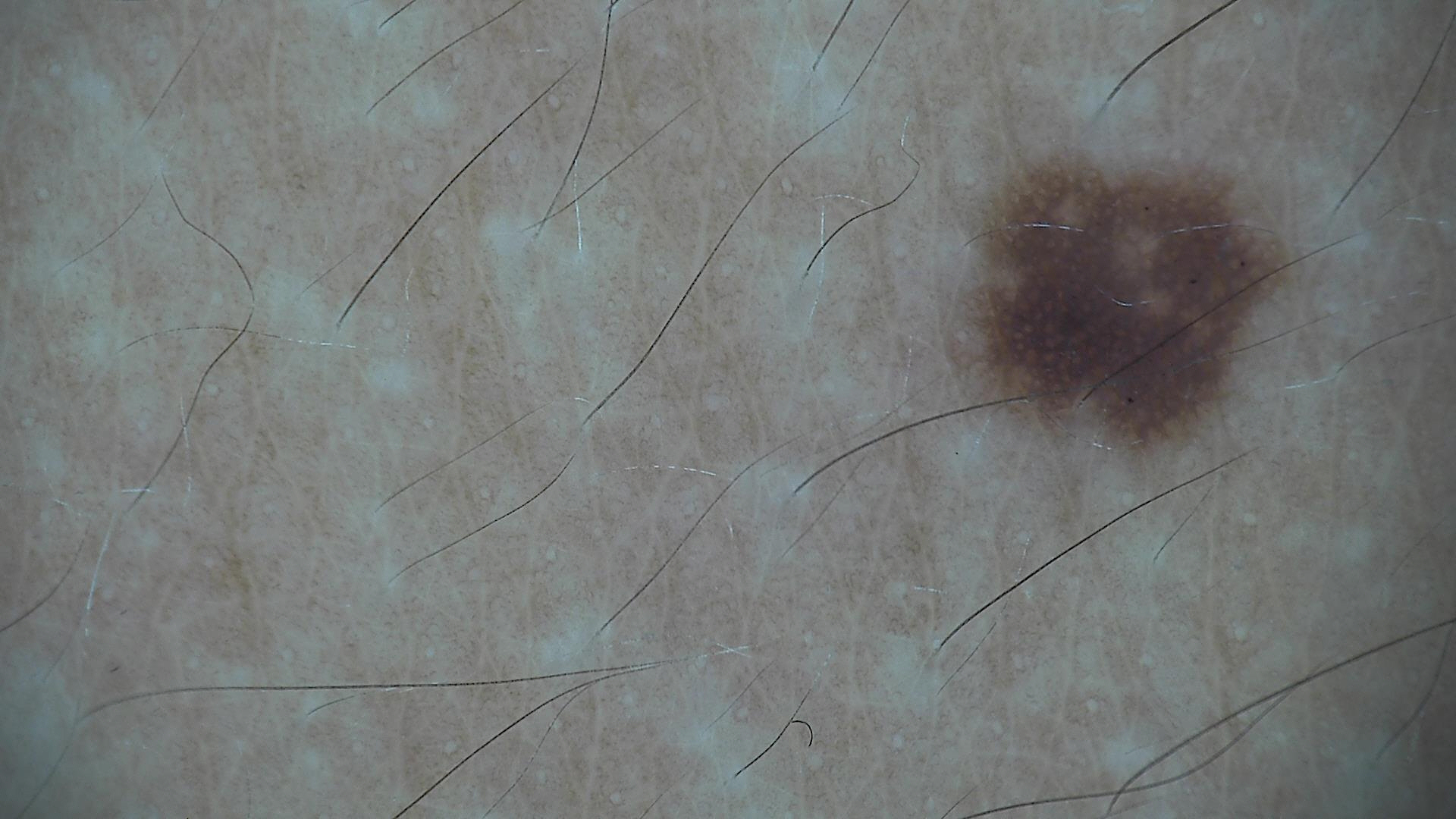diagnostic label: dysplastic junctional nevus (expert consensus).